A dermoscopic close-up of a skin lesion:
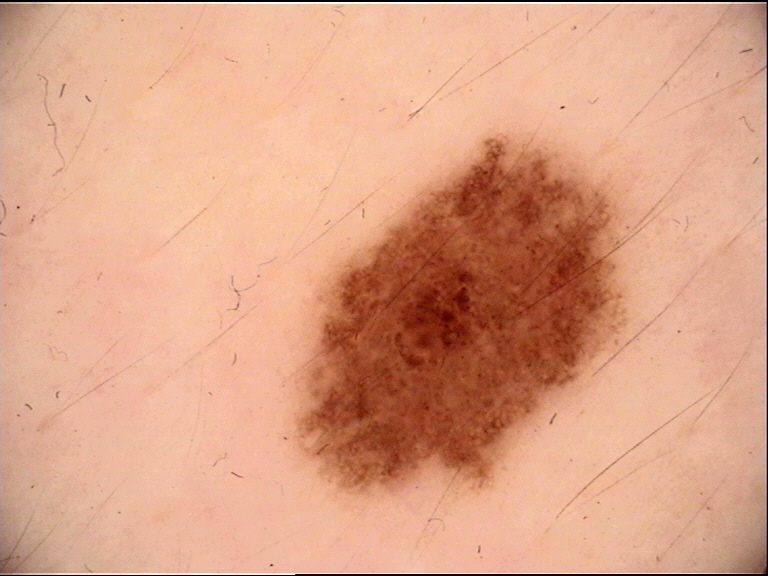- label — dysplastic junctional nevus (expert consensus)